Present for about one day. Self-categorized by the patient as a rash. Symptoms reported: itching. The patient notes the lesion is raised or bumpy. The lesion involves the arm. Close-up view. Skin tone: lay reviewers estimated 2 on the Monk skin tone scale — 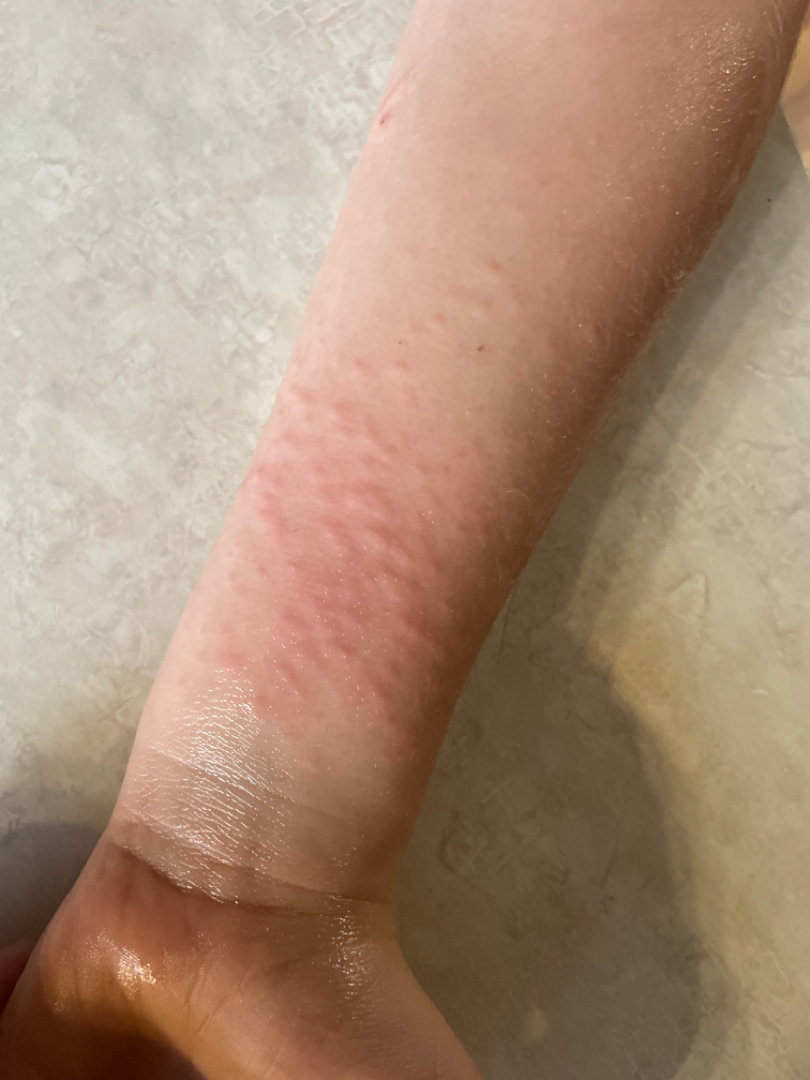Notes:
• differential diagnosis · Urticaria and Acute dermatitis, NOS were each considered, in no particular order